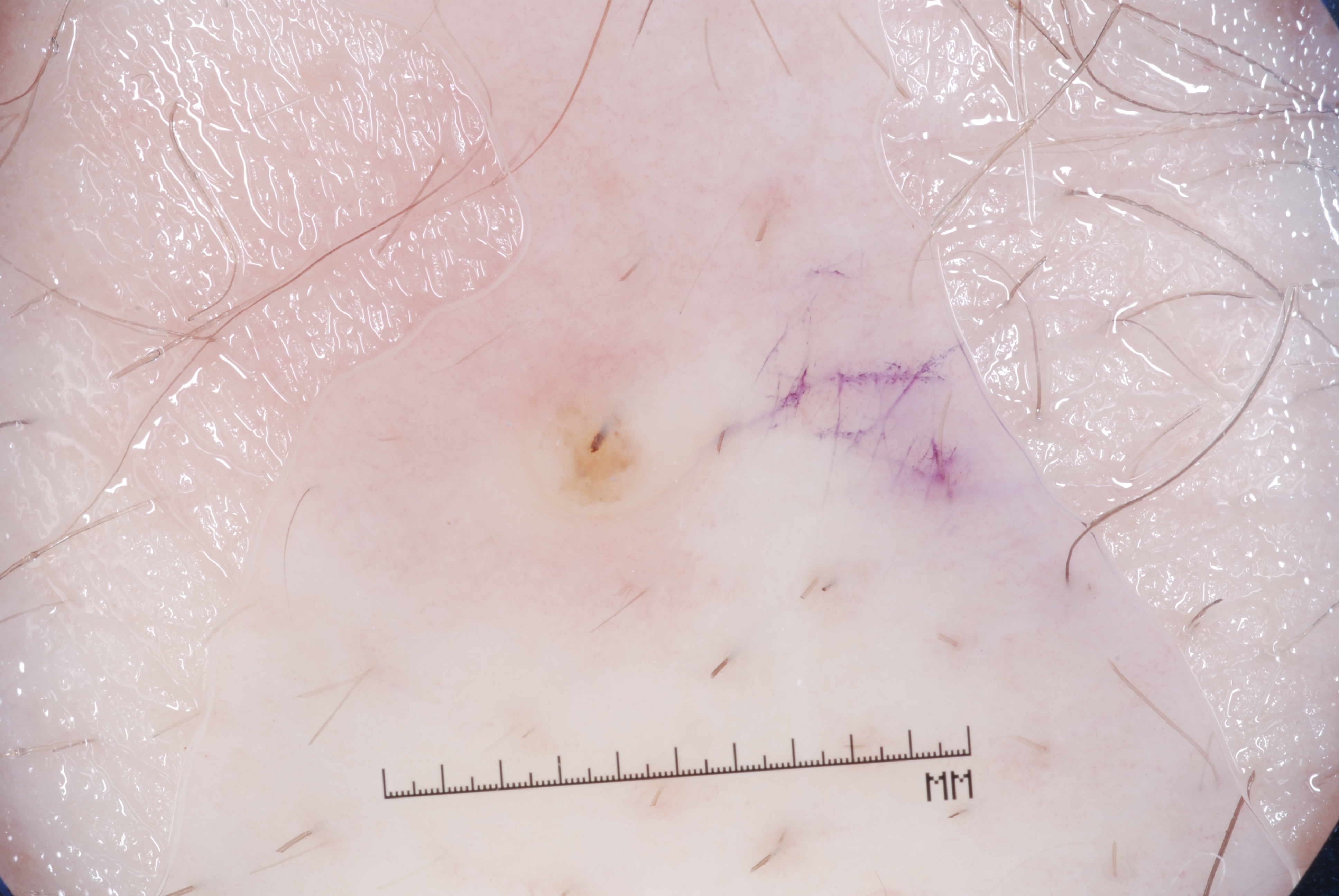modality — dermoscopy of a skin lesion; patient — male, about 40 years old; absent dermoscopic features — milia-like cysts, pigment network, negative network, and streaks; bounding box — [526,378,678,512]; extent — ~1% of the field; impression — a melanocytic nevus.